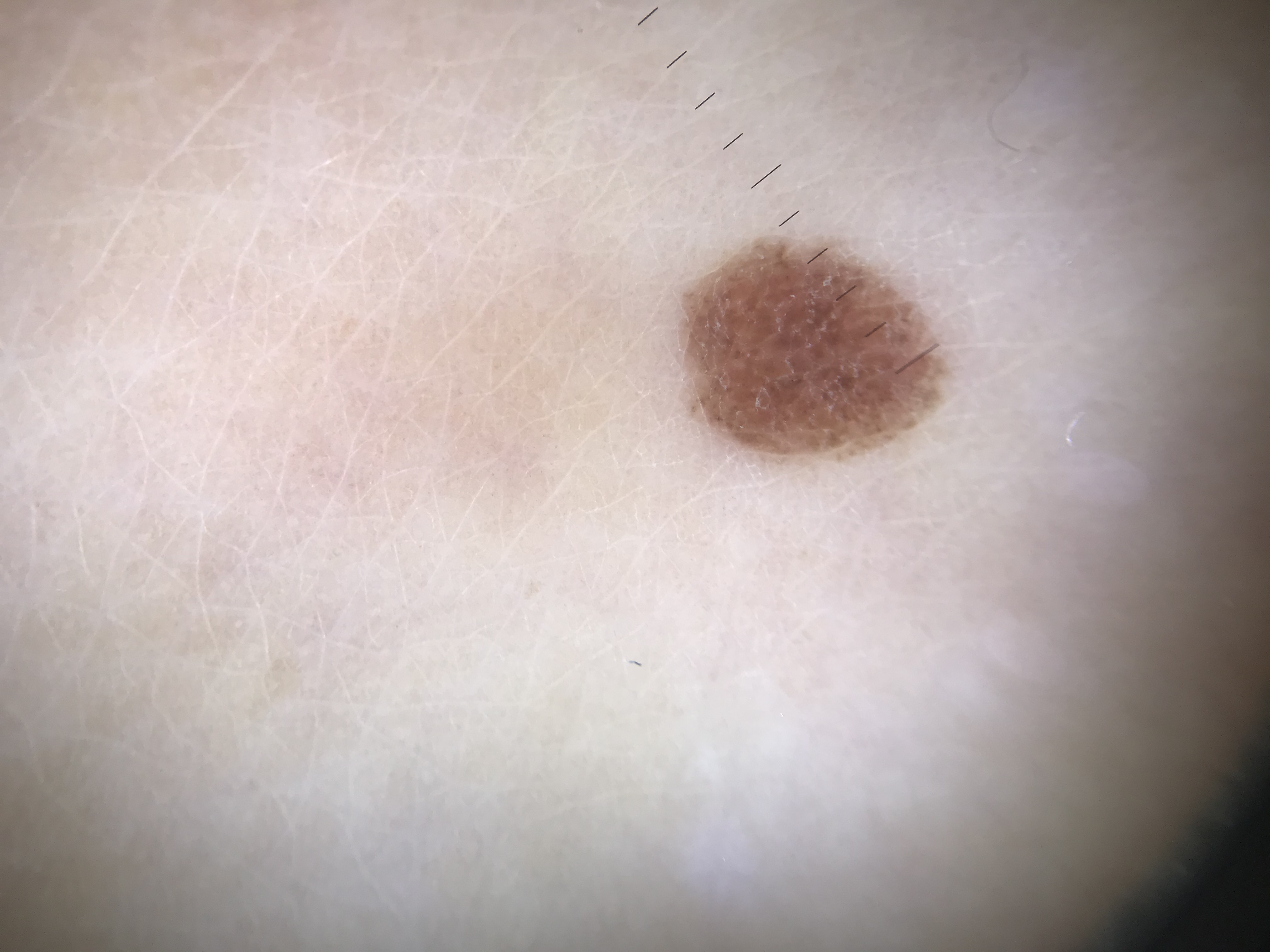Q: What kind of image is this?
A: dermatoscopy
Q: What was the diagnostic impression?
A: compound nevus (expert consensus)